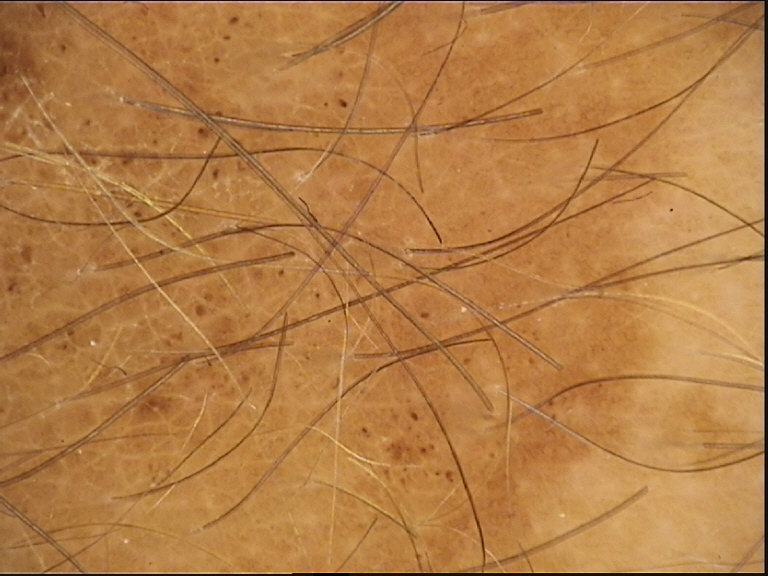image type=dermoscopy
class=congenital compound nevus (expert consensus)